A dermoscopy image of a single skin lesion: 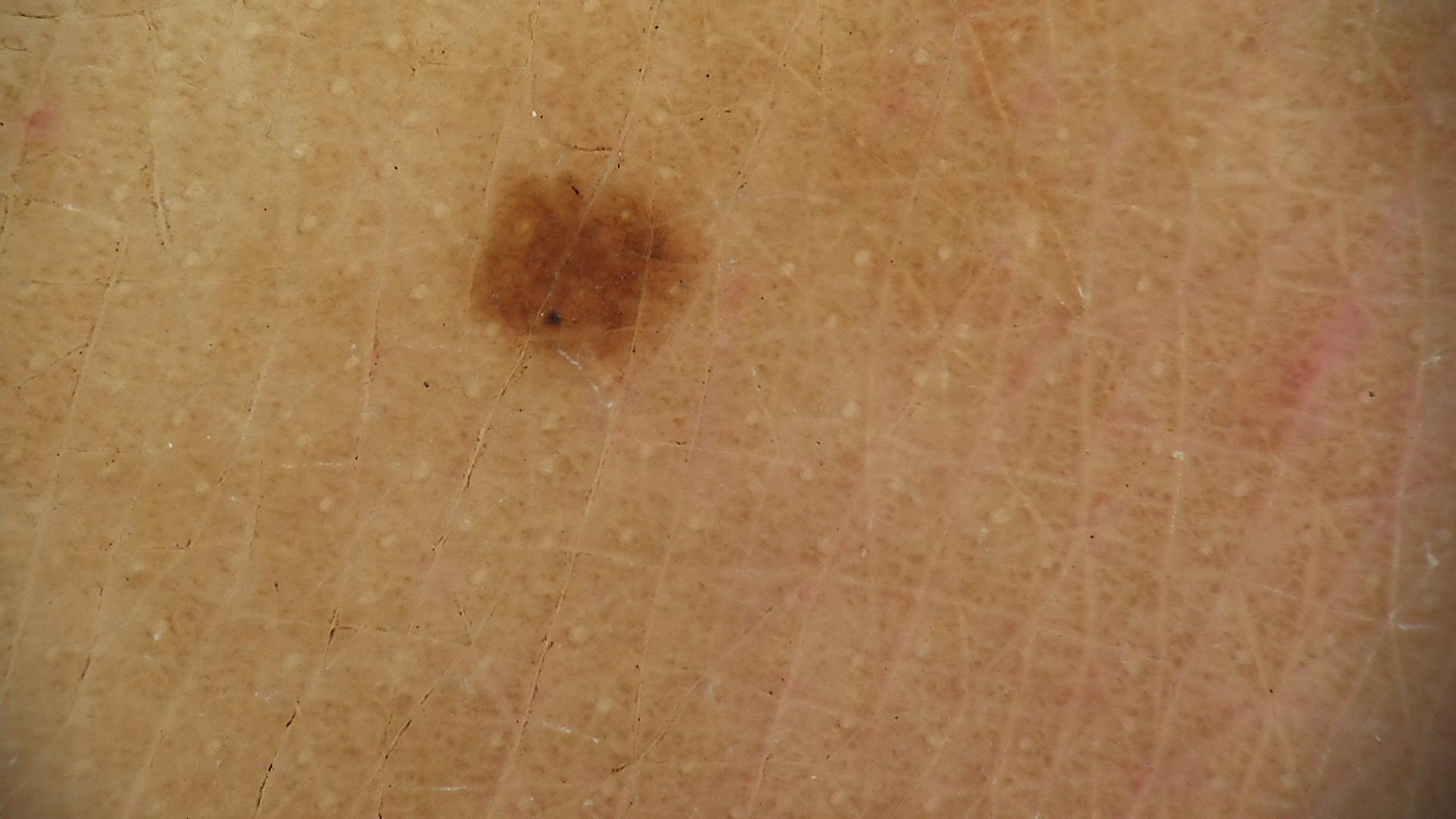The diagnosis was an acral dysplastic junctional nevus.